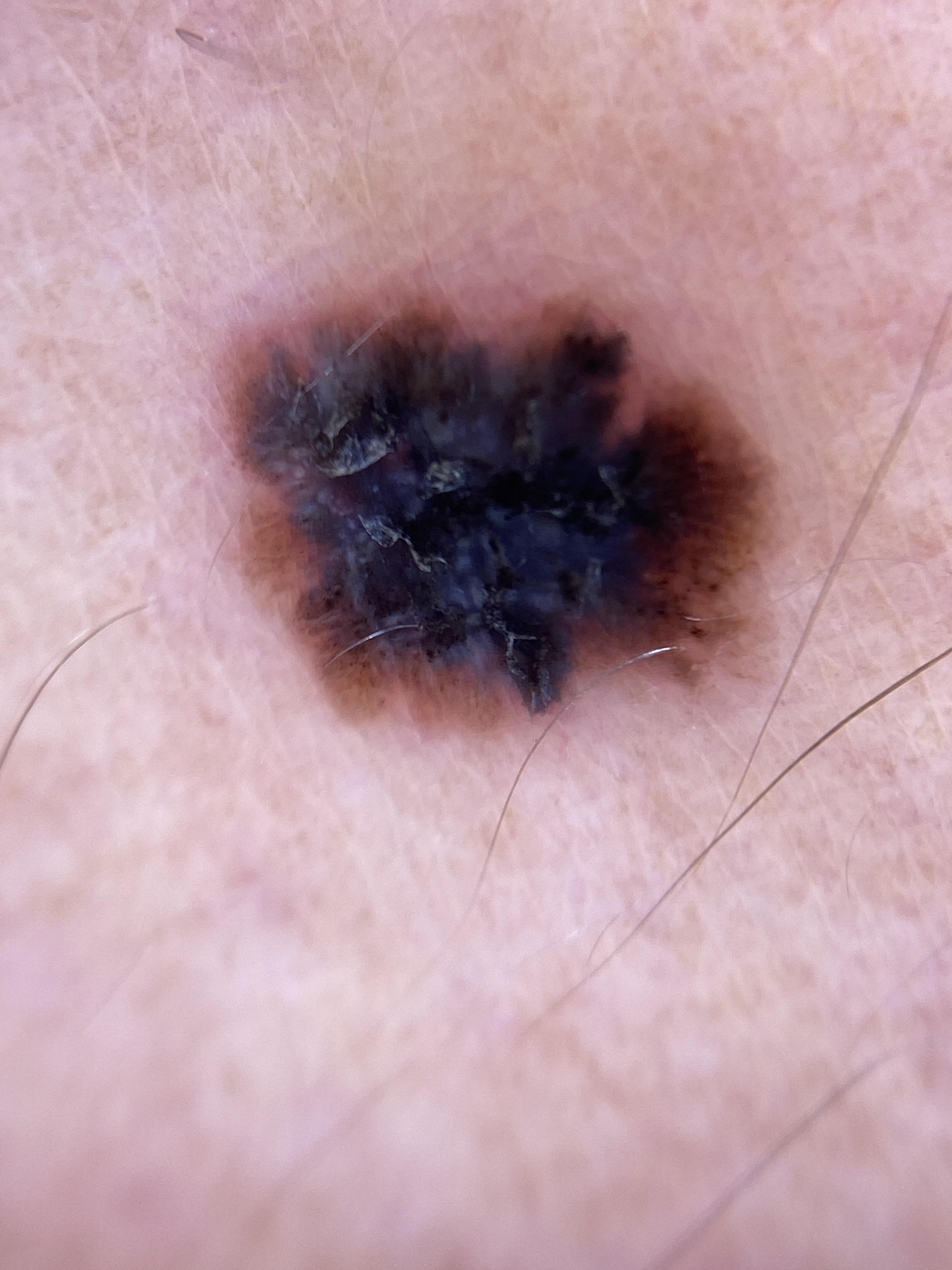risk factors = a previous melanoma | subject = female, aged 43 to 47 | image type = dermoscopy | anatomic site = an upper extremity | diagnosis = Melanoma (biopsy-proven).